A dermoscopy image of a single skin lesion: 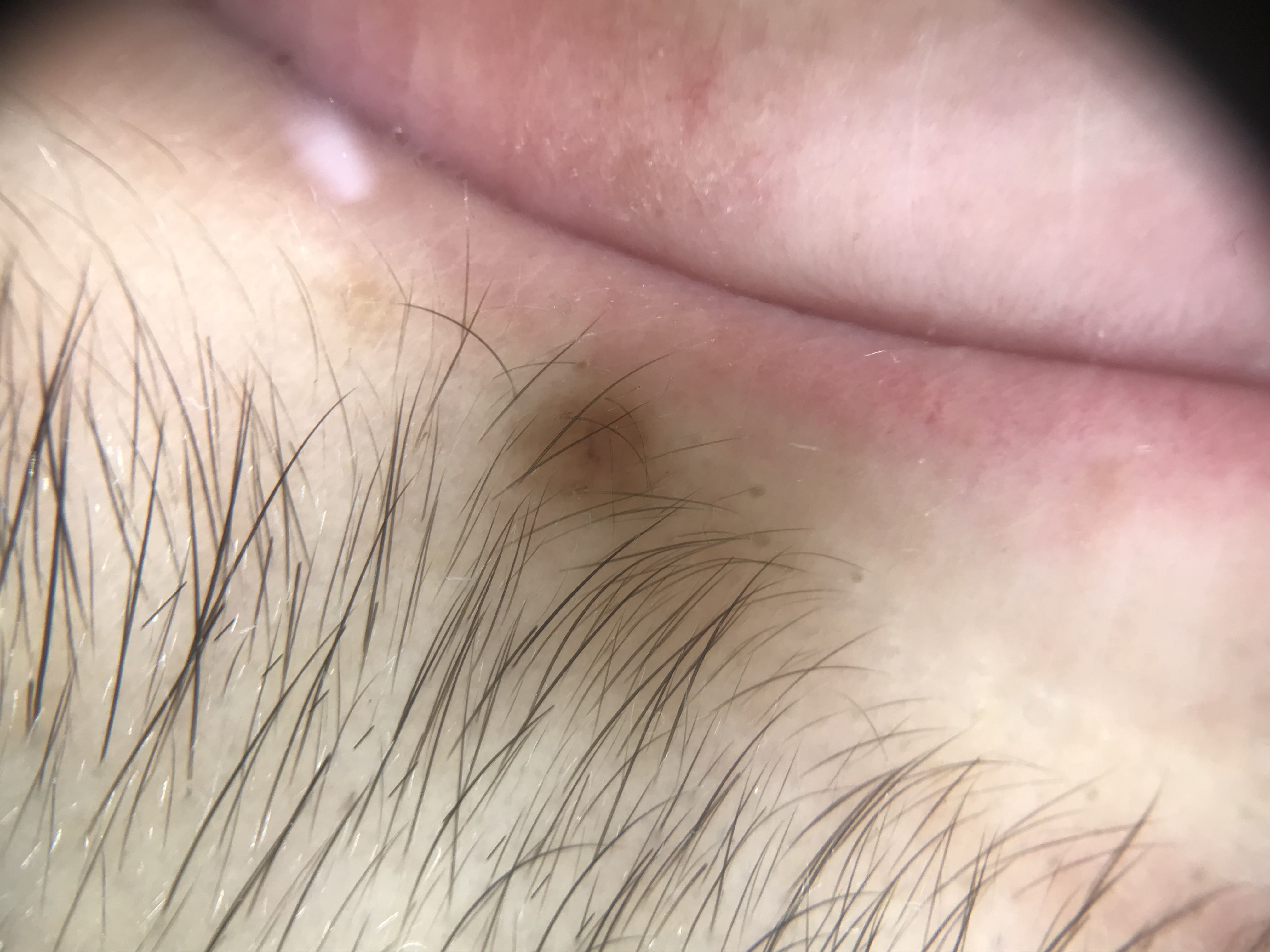assessment=Miescher nevus (expert consensus)